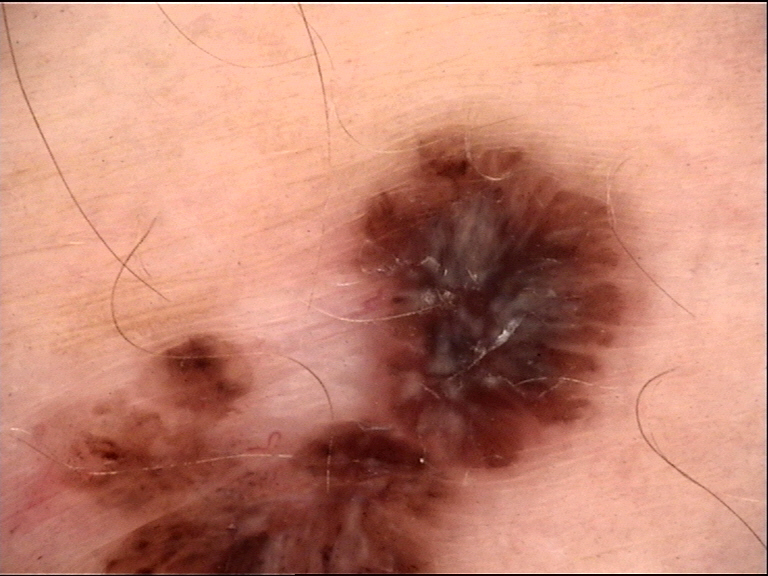The biopsy diagnosis was a malignant, keratinocytic lesion — a basal cell carcinoma.